The front of the torso and back of the hand are involved · female patient, age 30–39 · self-categorized by the patient as a rash · the contributor notes the lesion is raised or bumpy · reported lesion symptoms include itching and bothersome appearance · close-up view:
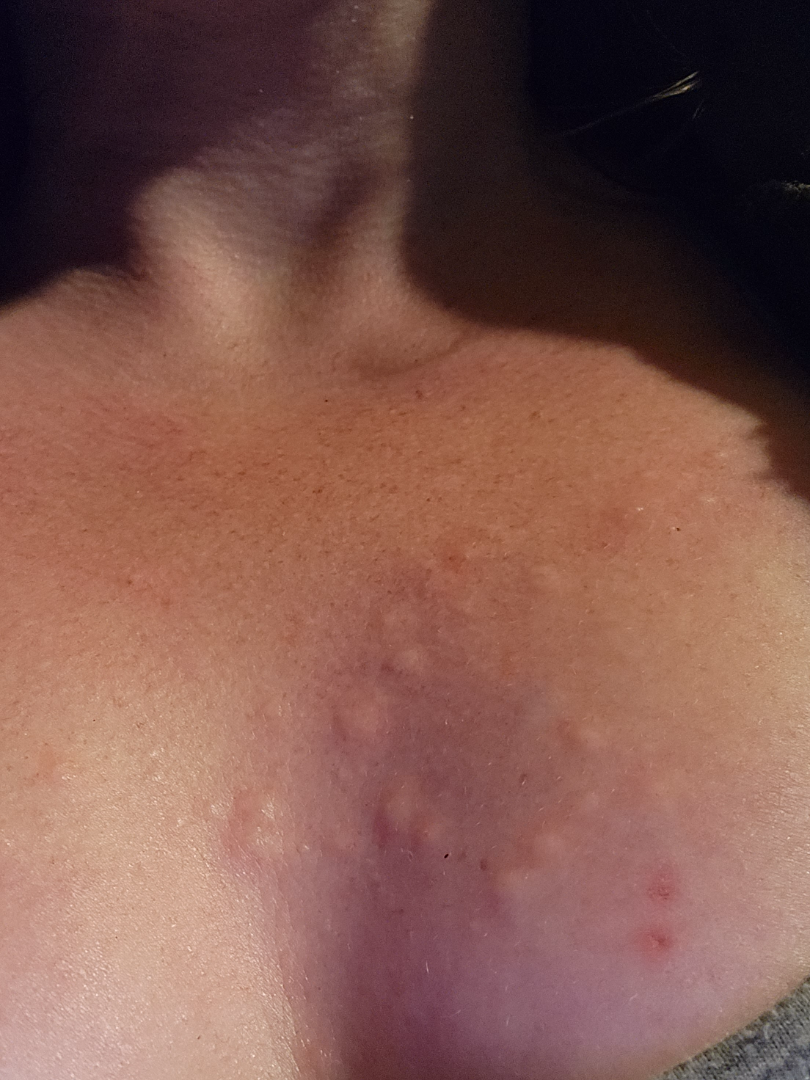Findings:
* assessment — ungradable on photographic review